Symptoms reported: itching and bothersome appearance. Reported duration is more than one year. The lesion is described as flat, rough or flaky, raised or bumpy and fluid-filled. Associated systemic symptoms include fatigue. A close-up photograph. Female patient, age 40–49. Located on the sole of the foot and top or side of the foot.
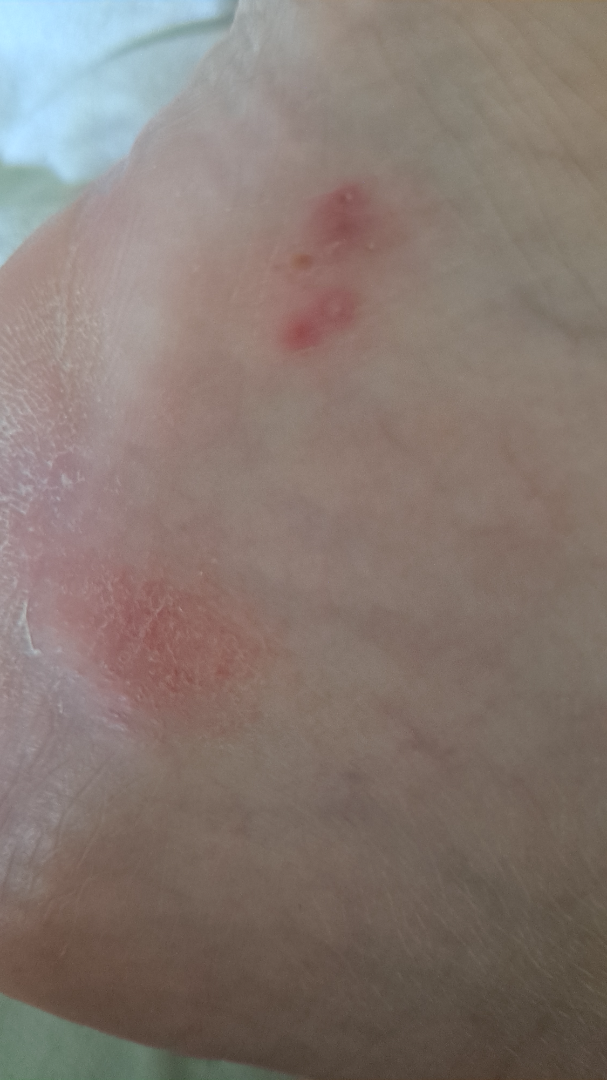Review:
The case was difficult to assess from the available photograph.